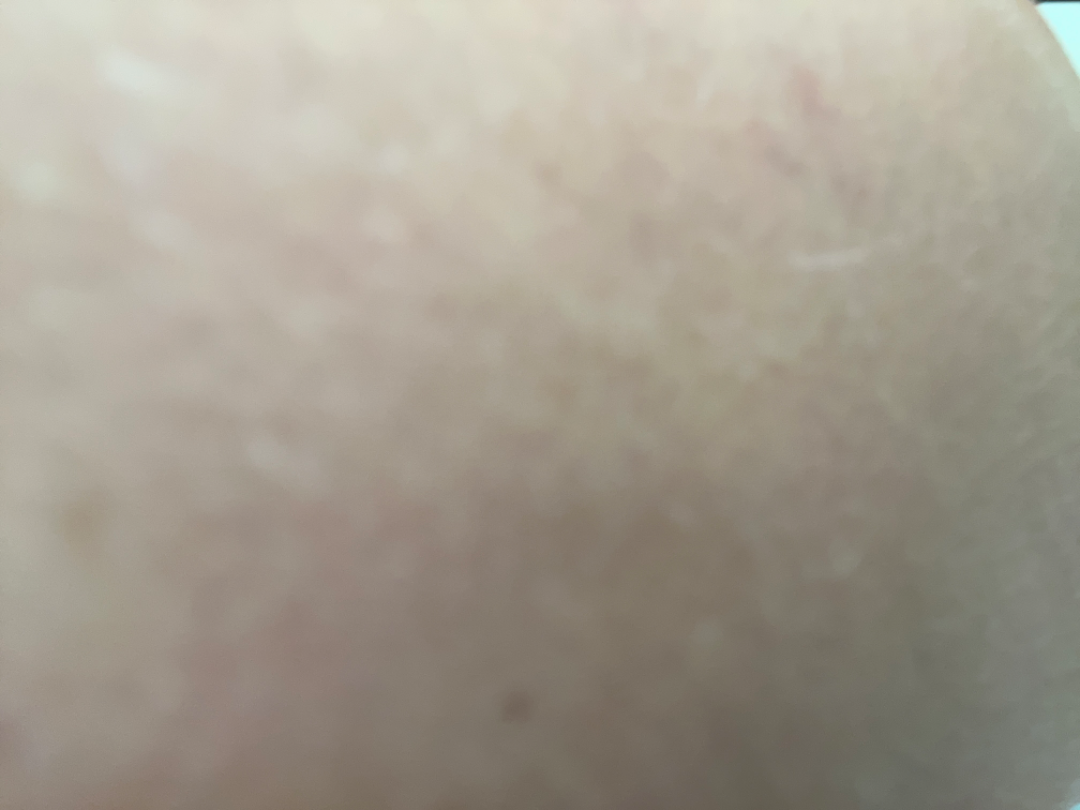Q: Age and sex?
A: female, age 40–49
Q: Anatomic location?
A: leg
Q: How was the photo taken?
A: at an angle
Q: What is the dermatologist's impression?
A: most likely Hypersensitivity; an alternative is Eczema